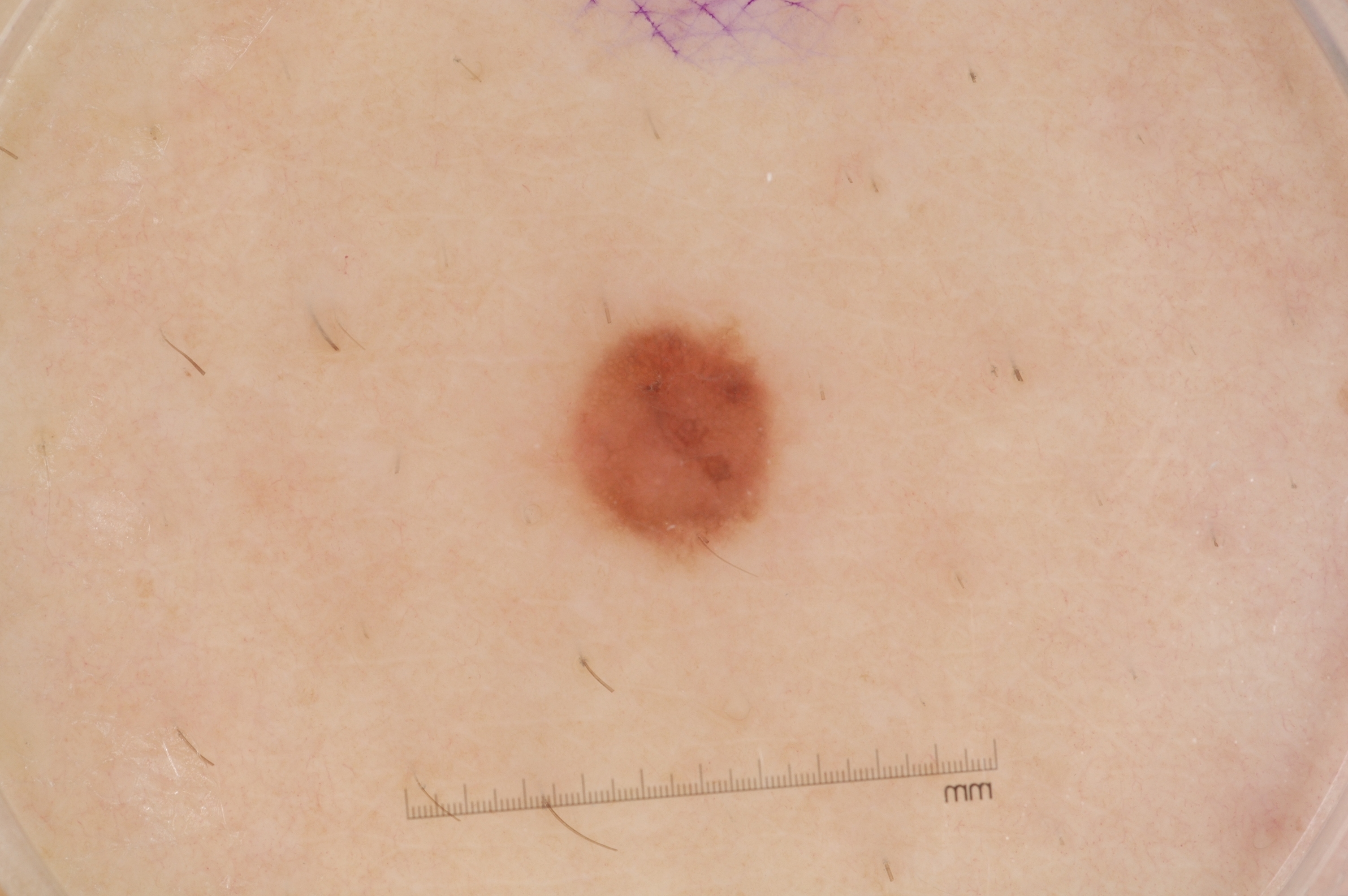Summary:
A dermatoscopic image of a skin lesion. The visible lesion spans x1=549, y1=308, x2=786, y2=565. Dermoscopic assessment notes milia-like cysts and pigment network; no streaks or negative network. A small lesion occupying a minor part of the field.
Impression:
Expert review diagnosed this as a melanocytic nevus, a benign skin lesion.